The photo was captured at an angle — 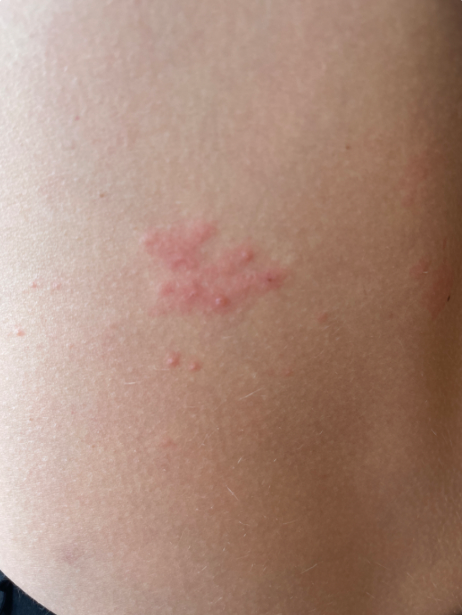differential:
  leading:
    - Herpes Simplex
  considered:
    - Insect Bite
    - Allergic Contact Dermatitis